The patient says their skin reddens with sun exposure. Collected as part of a research study, without a referral diagnosis. By self-report, a personal history of skin cancer and no personal history of cancer.
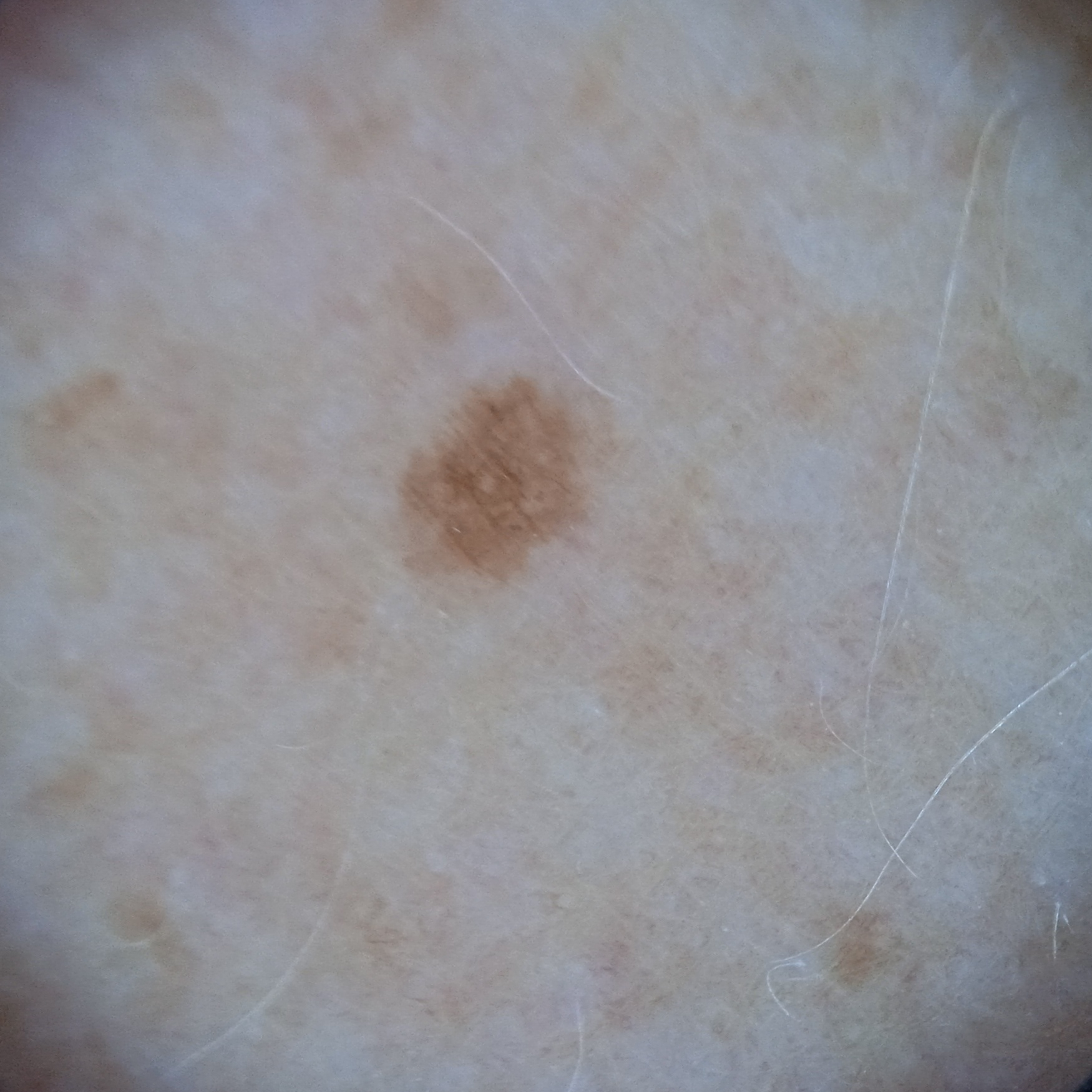The dermatologists' assessment was a melanocytic nevus.